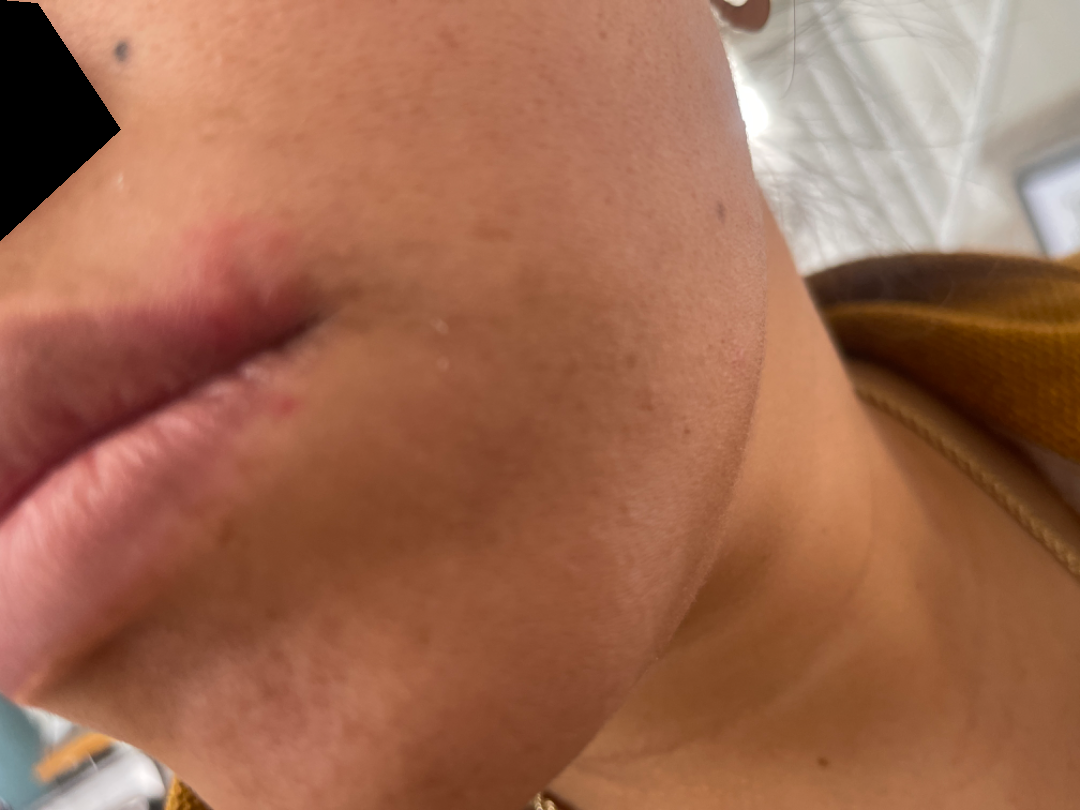Texture is reported as raised or bumpy. The lesion is associated with itching. An image taken at an angle. The patient reported no systemic symptoms. The condition has been present for about one day. The subject is 30–39, female. Herpes Simplex (most likely); Allergic Contact Dermatitis (considered).